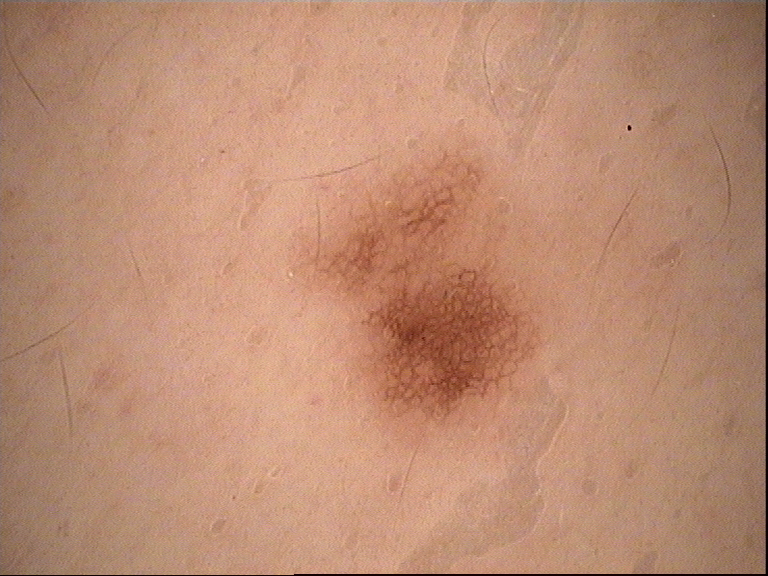A dermoscopic photograph of a skin lesion. The architecture is that of a banal lesion. Consistent with a junctional nevus.